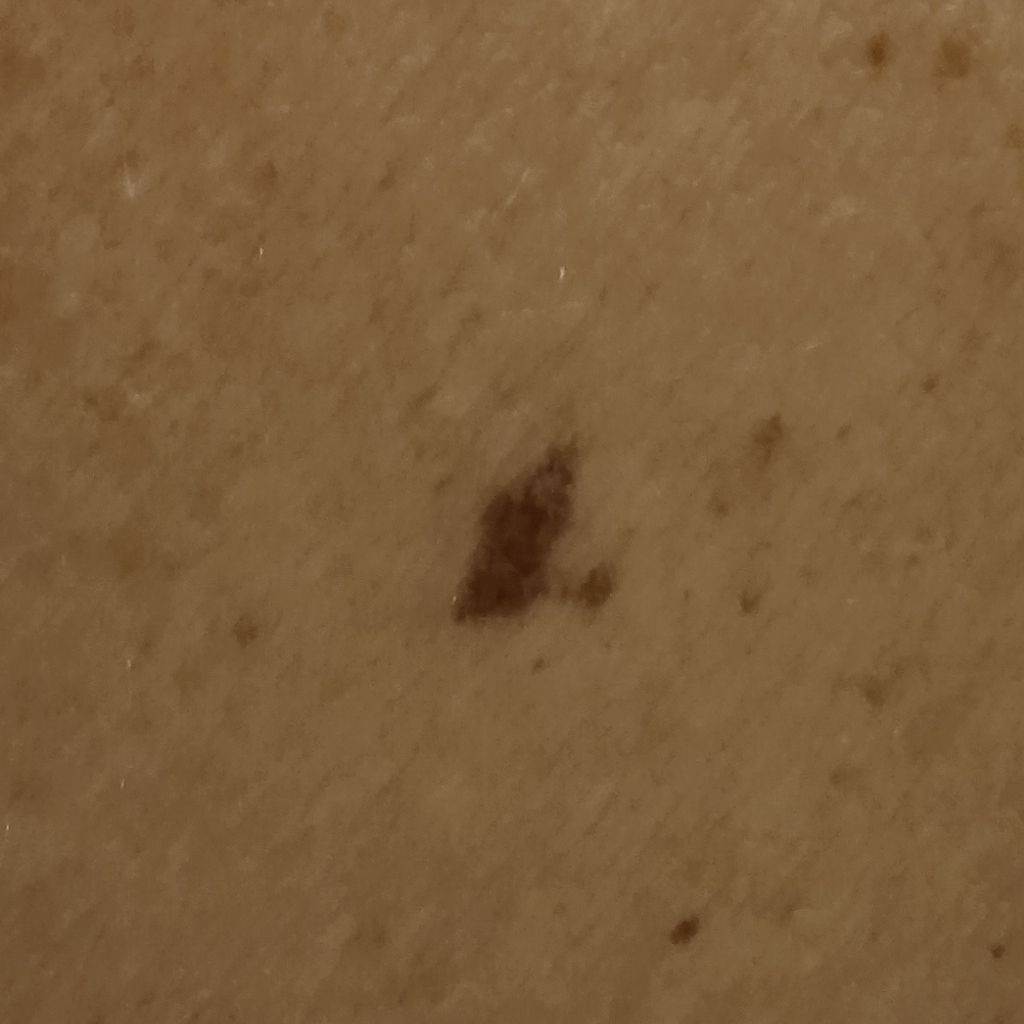Case:
* relevant history · a personal history of cancer, a family history of skin cancer
* referral · clinical suspicion of melanocytic nevus
* modality · clinical photo
* sun reaction · skin tans without first burning
* subject · female, aged 64
* size · 8.3 mm
* diagnosis · atypical (dysplastic) nevus — biopsy-proven